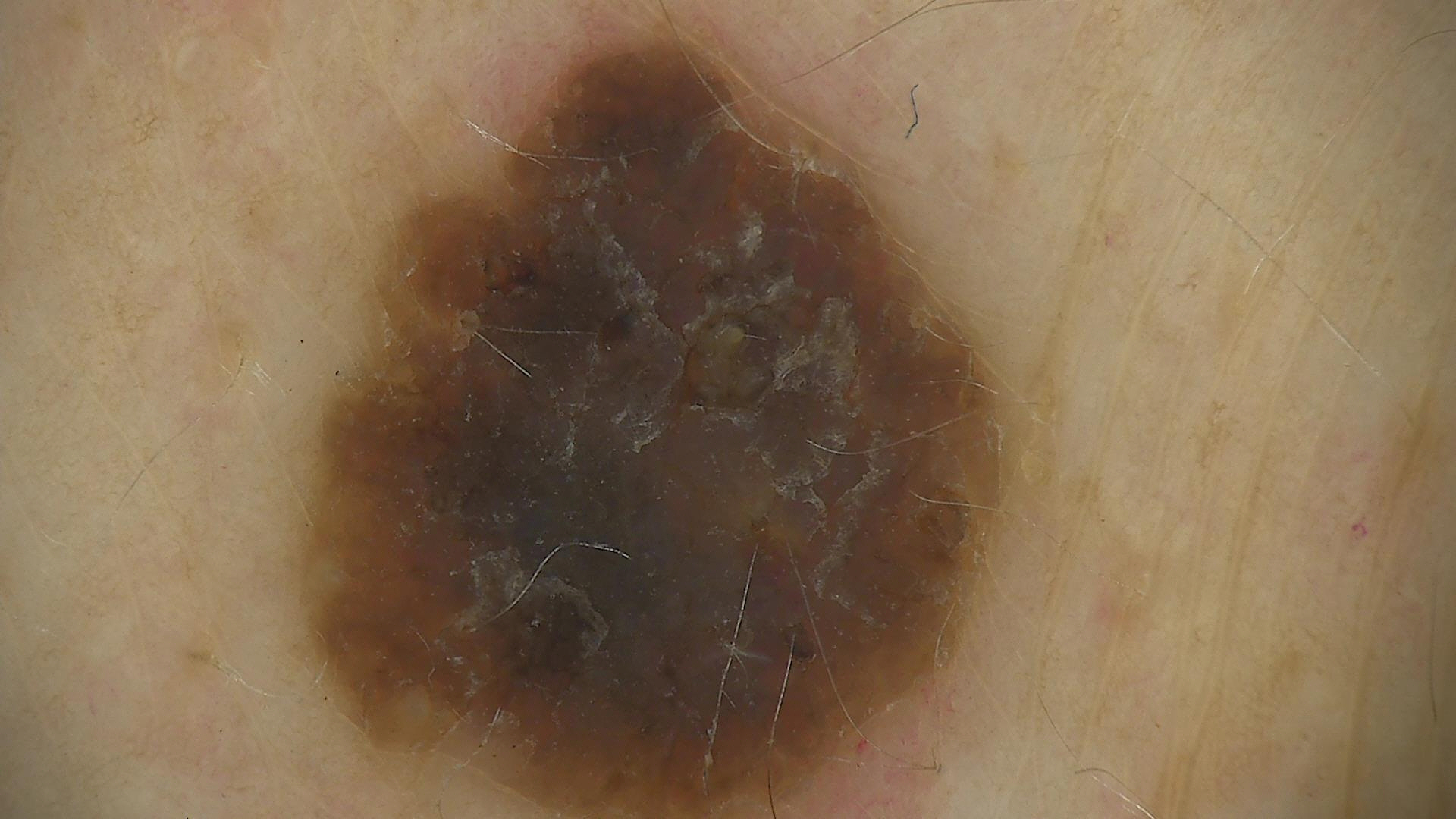Labeled as a seborrheic keratosis.